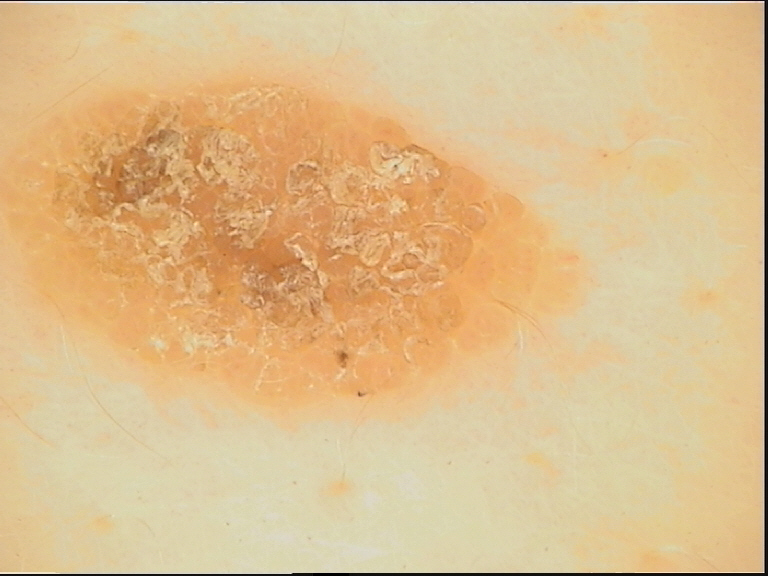A dermoscopic photograph of a skin lesion. The morphology is that of a keratinocytic lesion. The diagnosis was a benign lesion — a seborrheic keratosis.